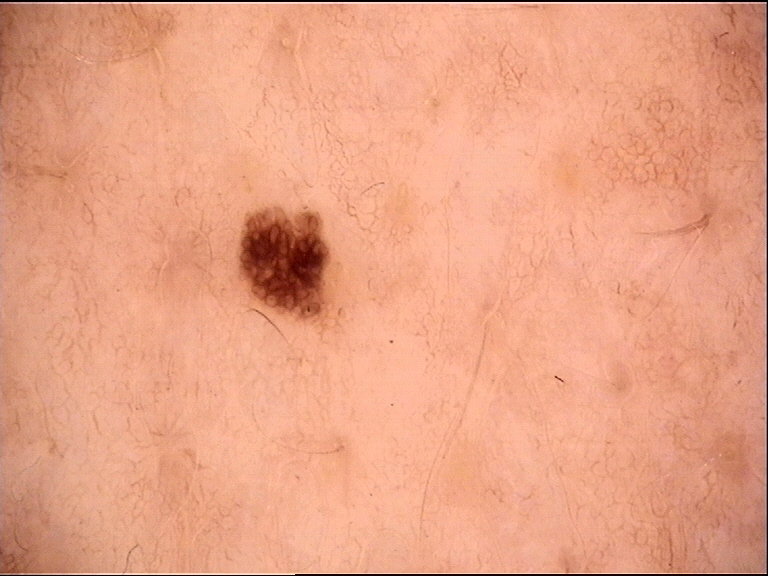A dermoscopic image of a skin lesion. Labeled as a dysplastic junctional nevus.